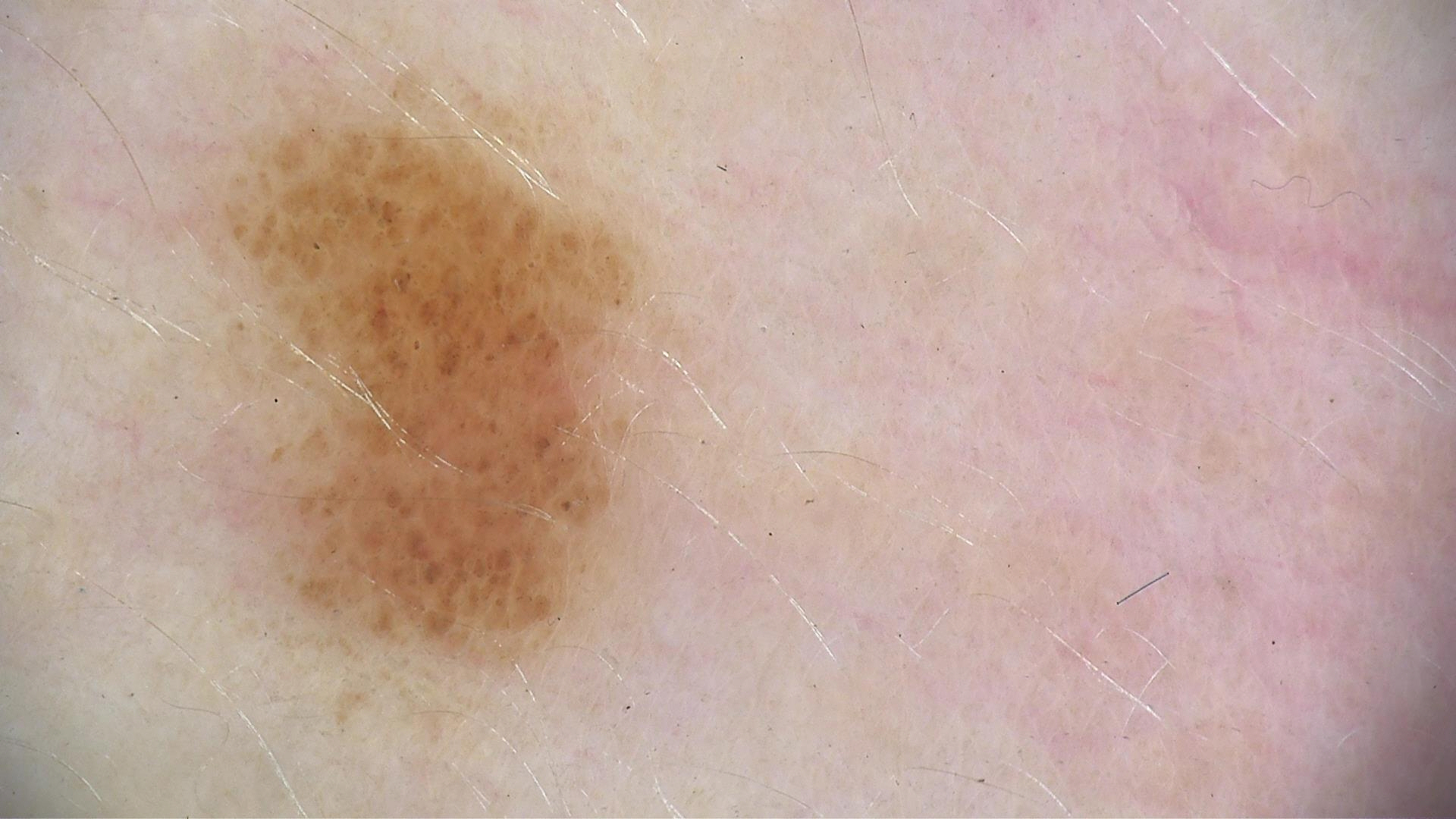| feature | finding |
|---|---|
| category | banal |
| label | compound nevus (expert consensus) |